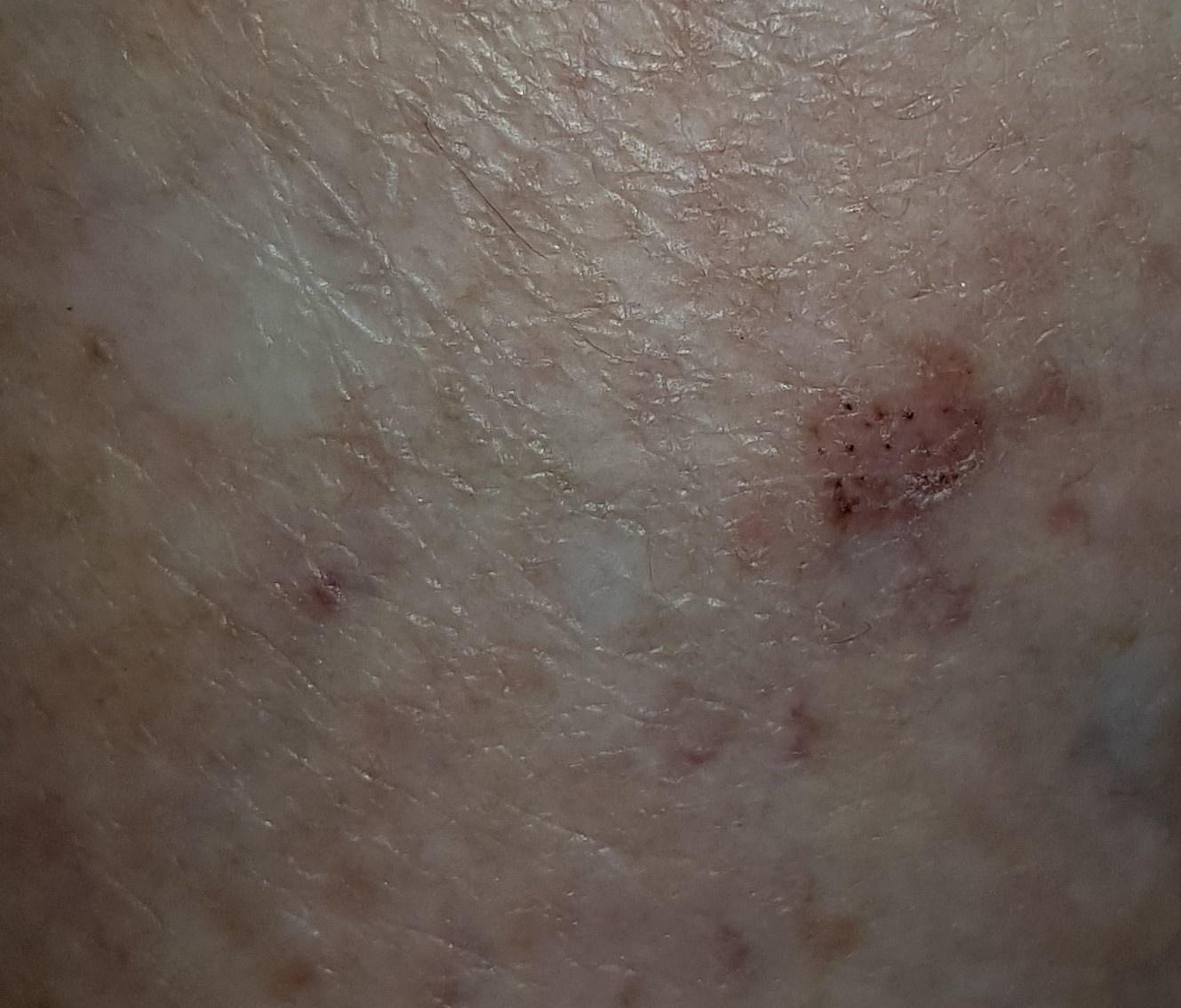Histopathology confirmed a basal cell carcinoma.